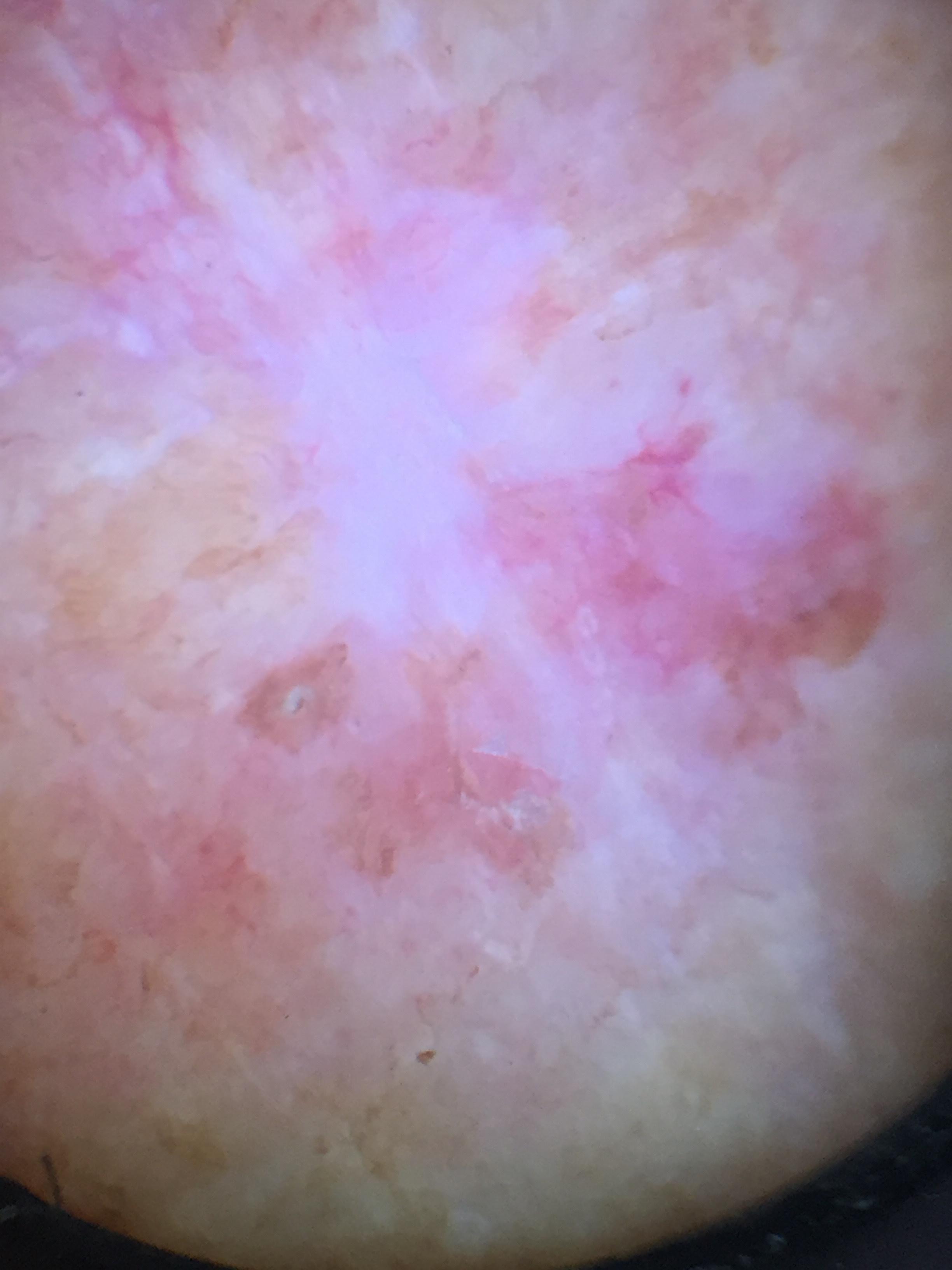A female patient in their mid- to late 80s or older. The patient was assessed as skin type II. Contact-polarized dermoscopy of a skin lesion. The lesion involves the head or neck. Histopathological examination showed a squamous cell carcinoma.